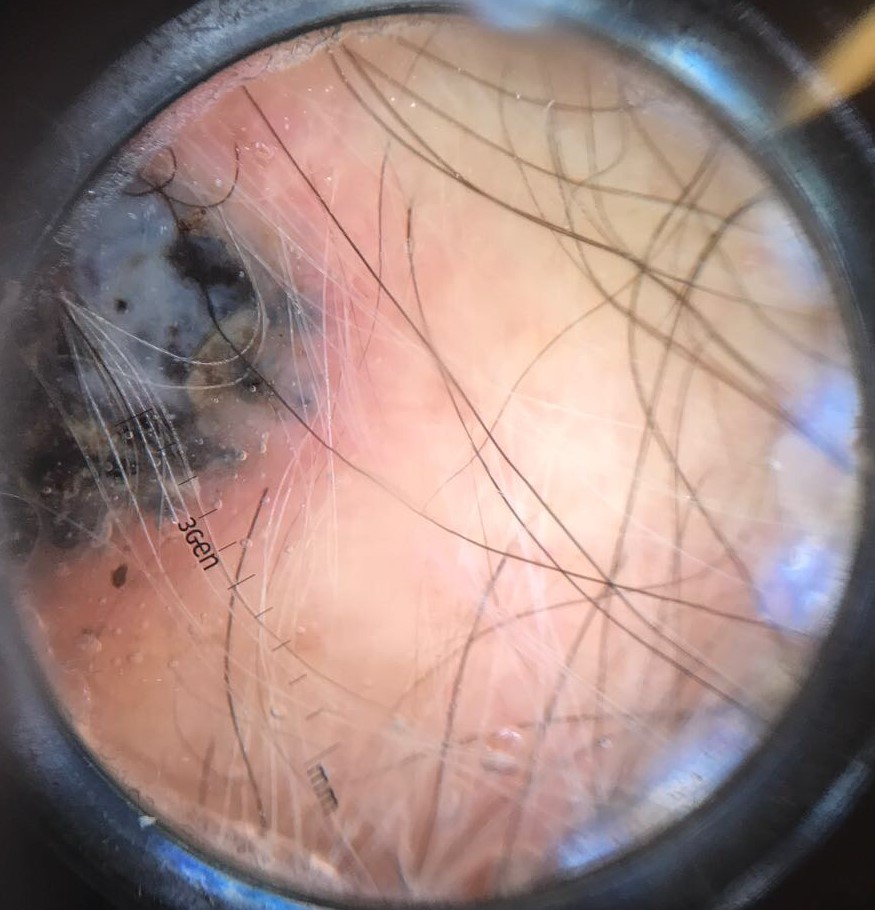modality=dermatoscopy | label=melanoma (biopsy-proven).